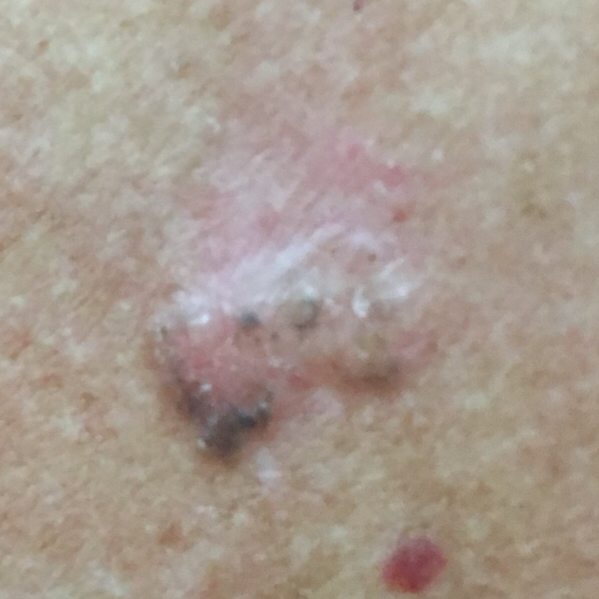| feature | finding |
|---|---|
| diagnosis | basal cell carcinoma (biopsy-proven) |